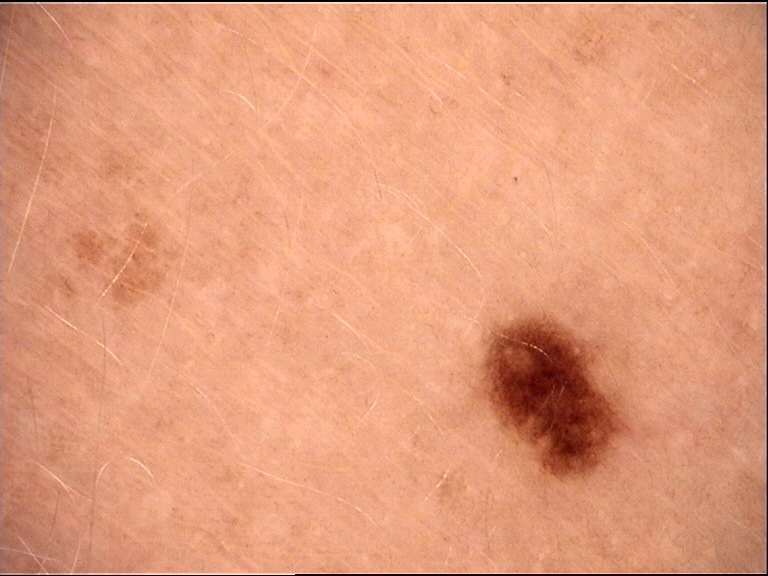image type=dermoscopy; assessment=dysplastic junctional nevus (expert consensus).